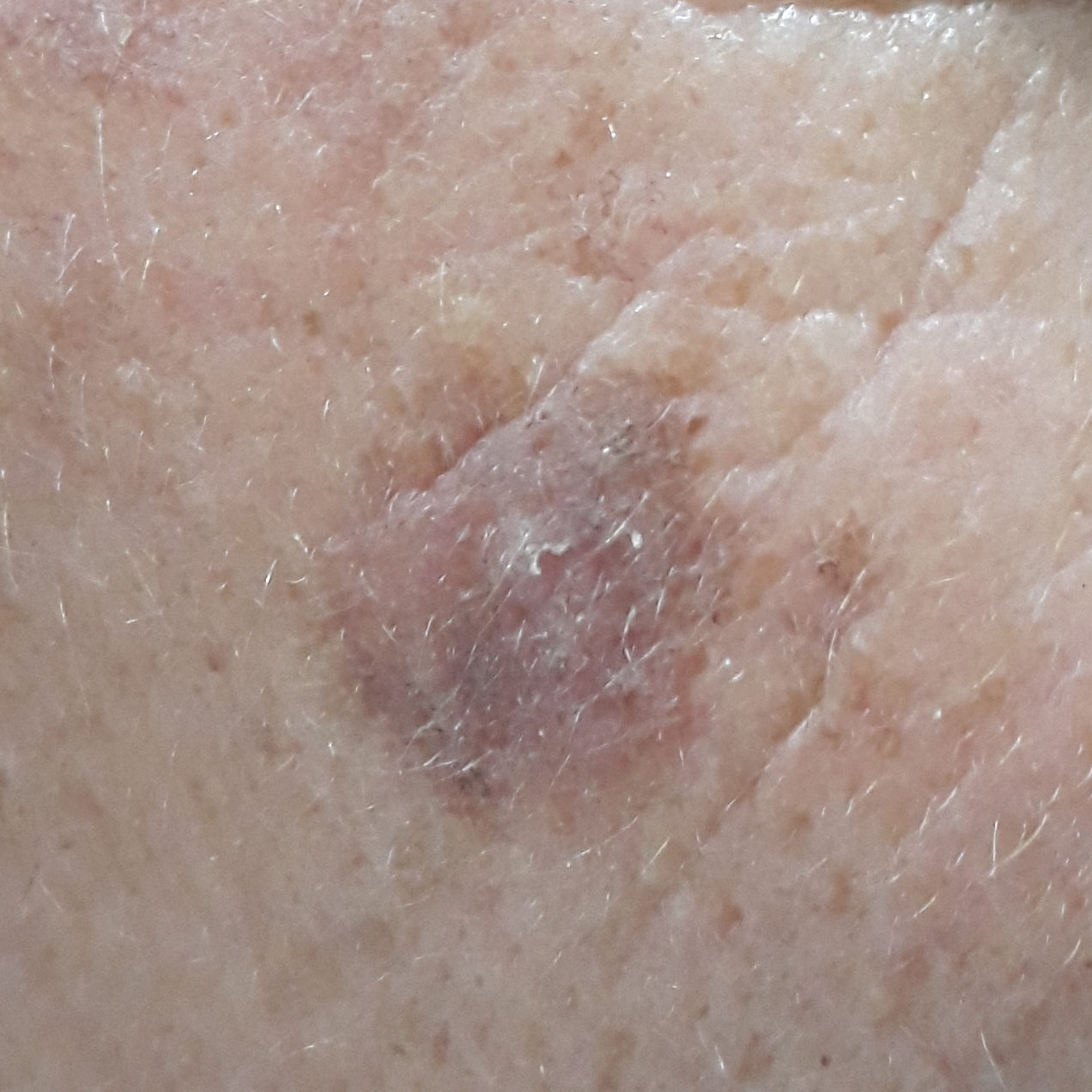Clinical context:
A clinical photograph of a skin lesion. A subject 53 years of age. Located on the face. The patient reports that the lesion has not grown and does not itch.
Conclusion:
The clinical impression was an actinic keratosis.